A male patient, about 15 years old. A dermoscopic close-up of a skin lesion: 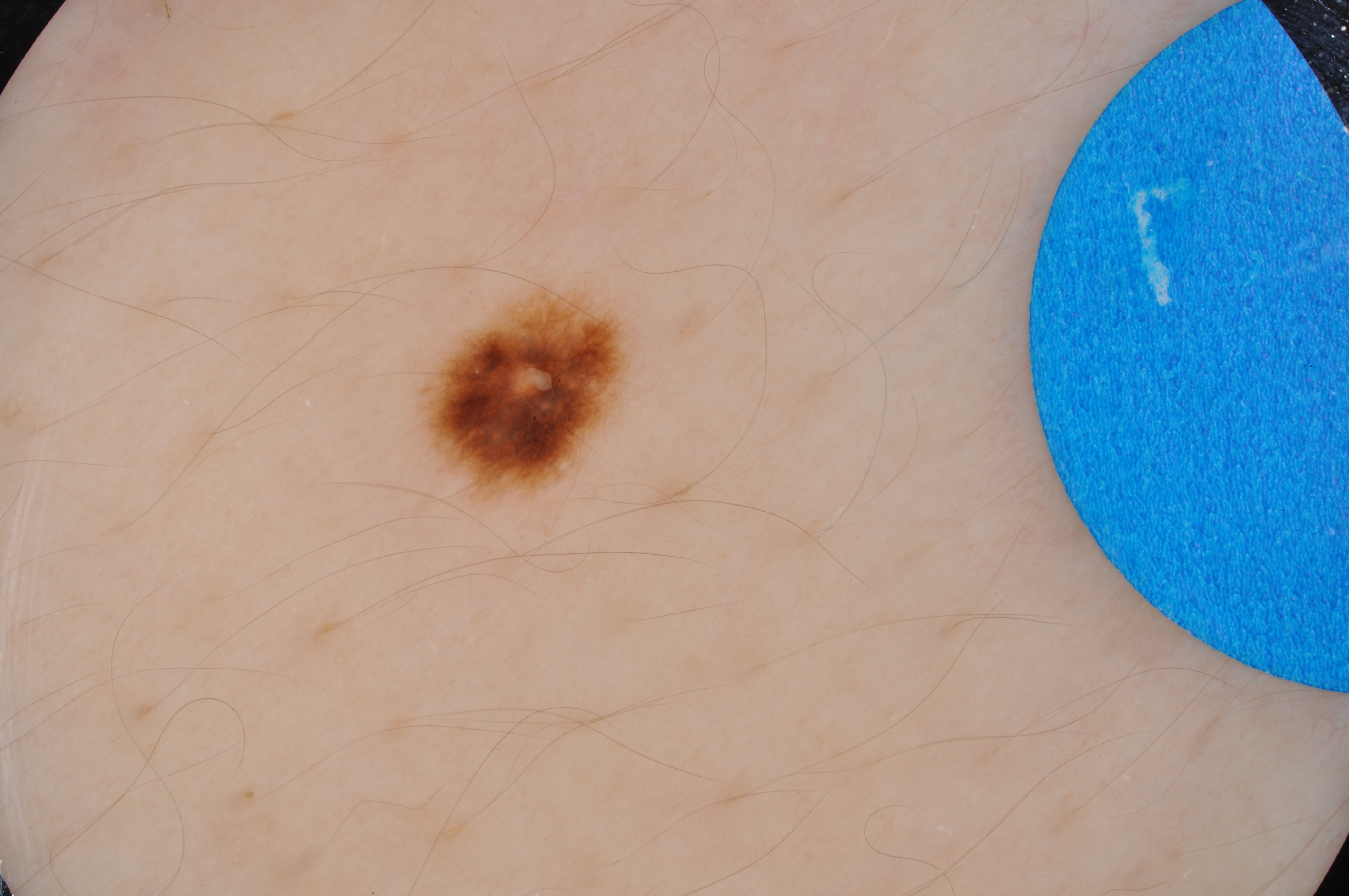{
  "lesion_location": {
    "bbox_xyxy": [
      406,
      270,
      633,
      519
    ]
  },
  "lesion_extent": {
    "approx_field_fraction_pct": 4
  },
  "dermoscopic_features": {
    "present": [
      "pigment network",
      "milia-like cysts"
    ],
    "absent": [
      "streaks",
      "negative network"
    ]
  },
  "diagnosis": {
    "name": "melanocytic nevus",
    "malignancy": "benign",
    "lineage": "melanocytic",
    "provenance": "clinical"
  }
}